Dermoscopy of a skin lesion:
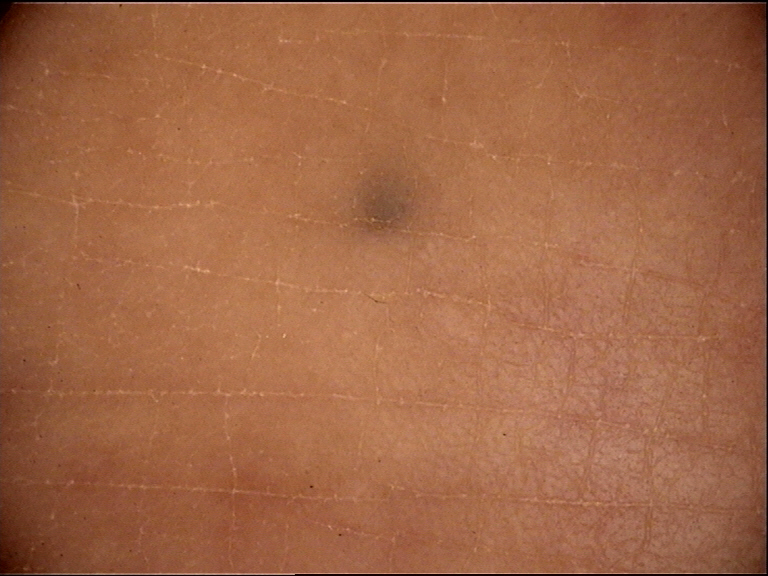Classified as a banal lesion — a blue nevus.